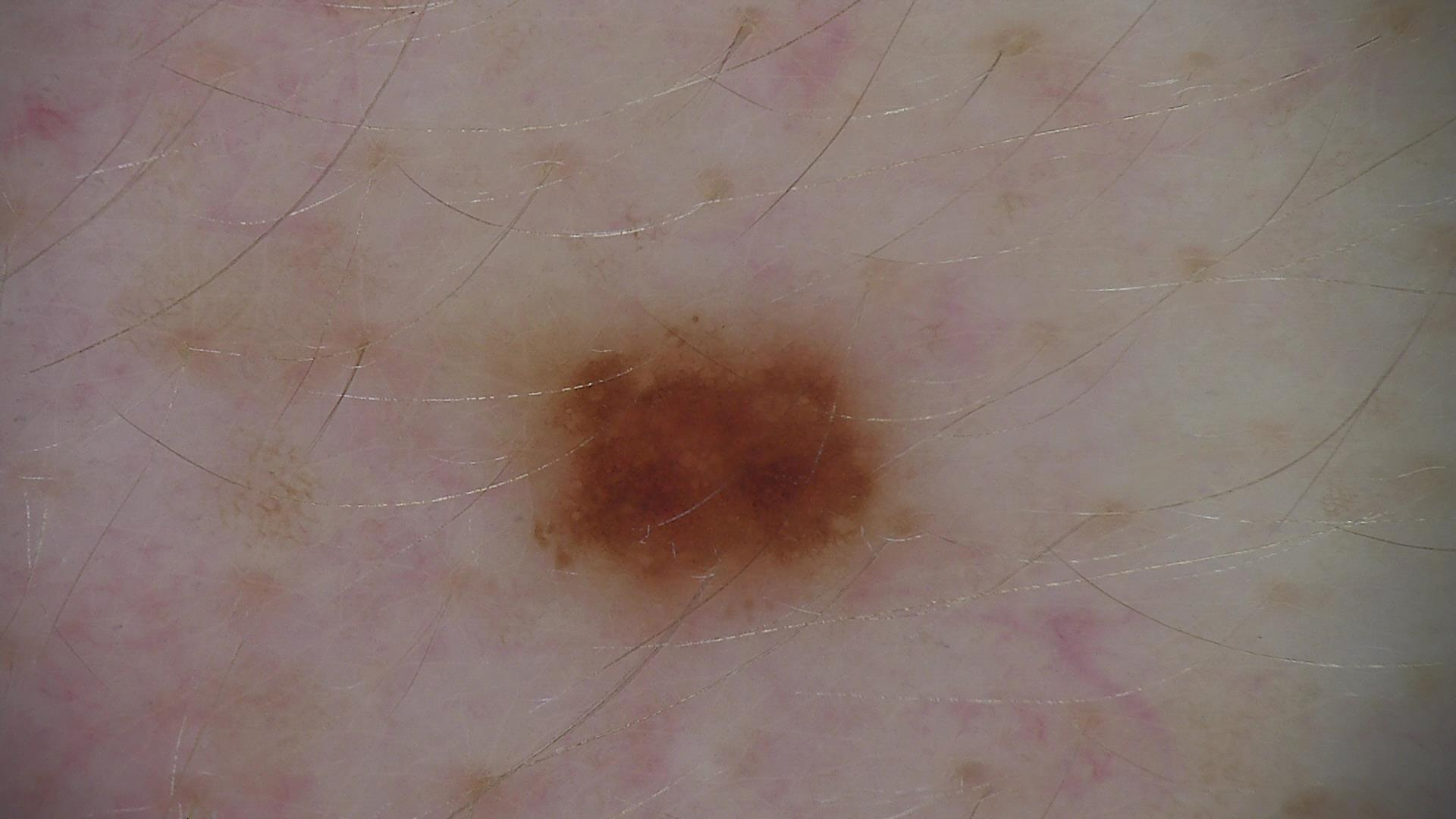Consistent with a dysplastic junctional nevus.